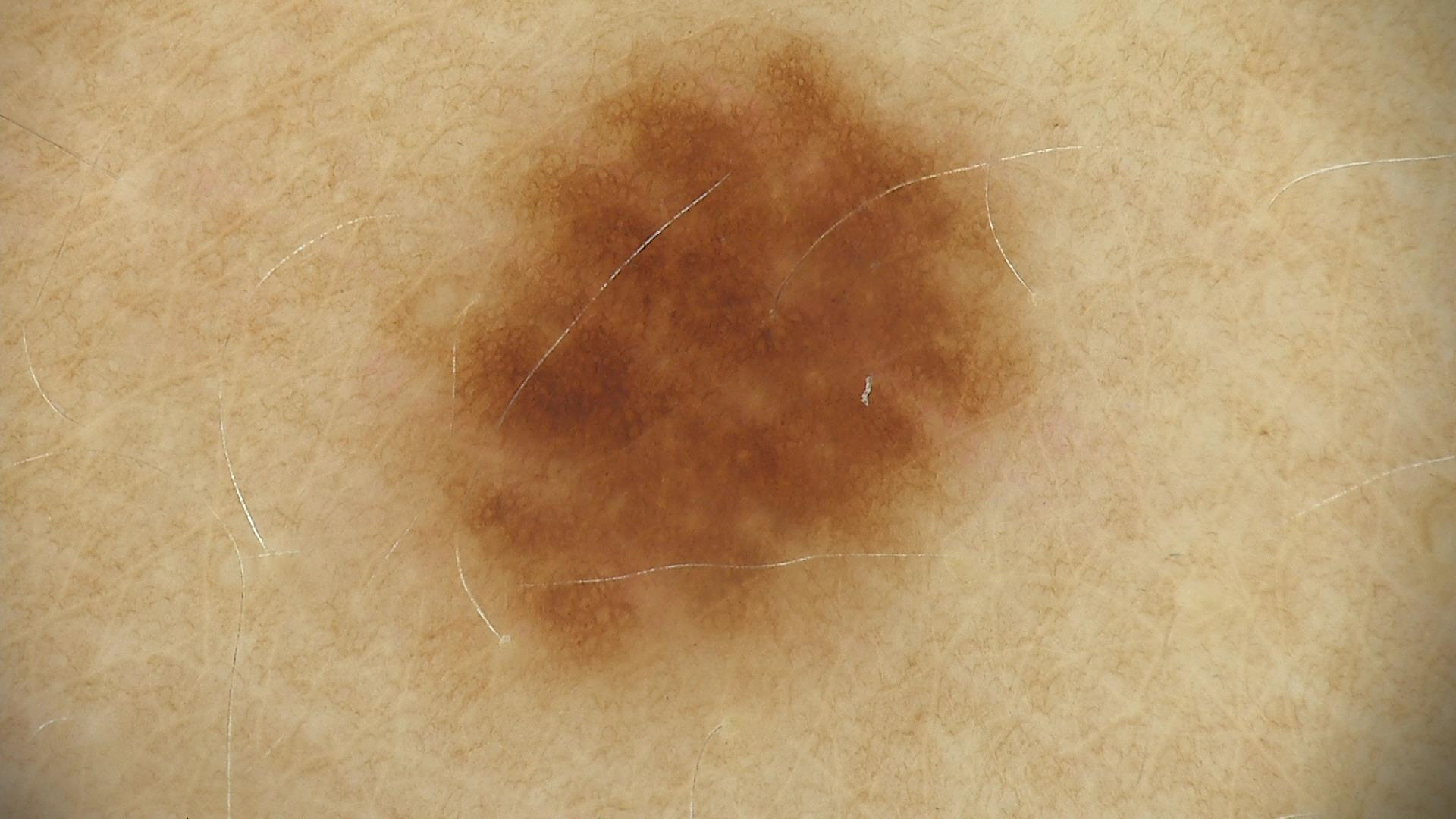class: dysplastic junctional nevus (expert consensus).